The leg is involved; female patient, age 30–39; this is a close-up image:
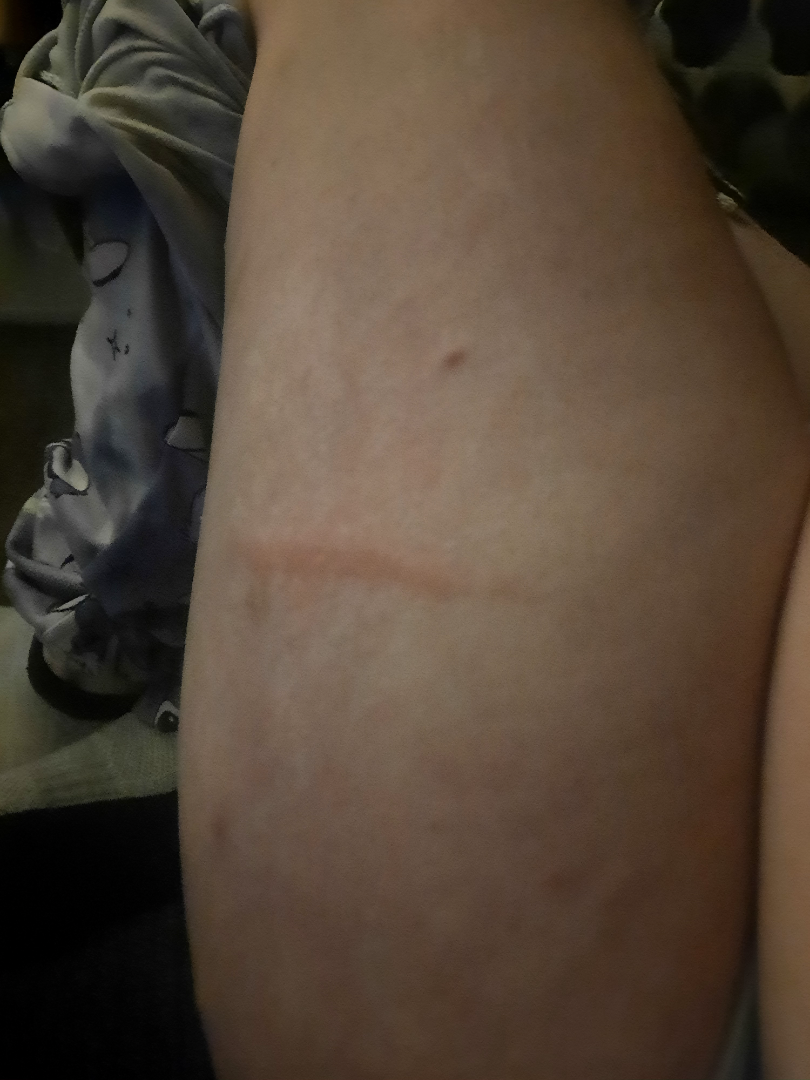<case>
<assessment>no discernible pathology</assessment>
<patient_category>a rash</patient_category>
<duration>about one day</duration>
<symptoms>itching</symptoms>
</case>